A dermoscopic close-up of a skin lesion.
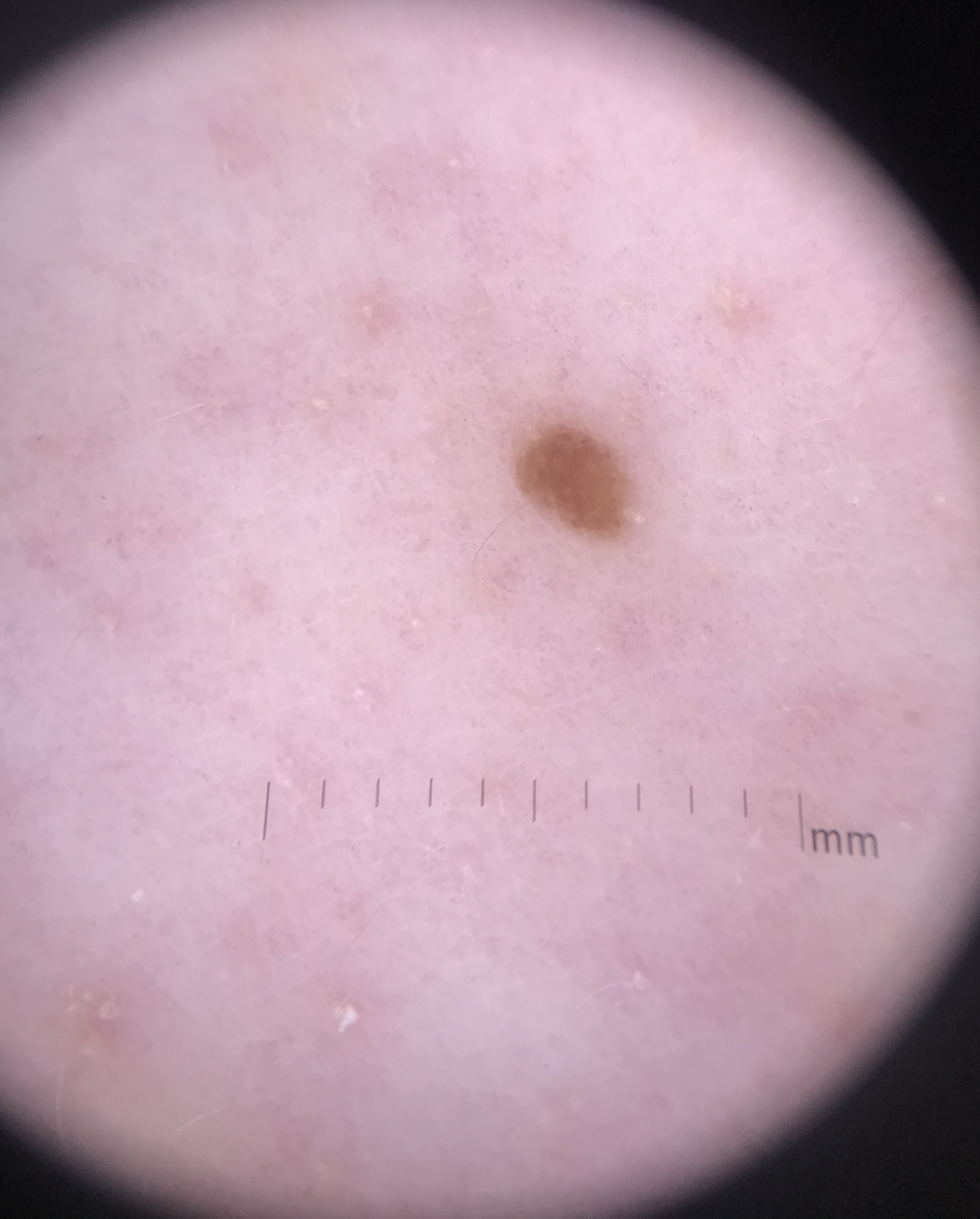subtype=keratinocytic | diagnosis=seborrheic keratosis (expert consensus).